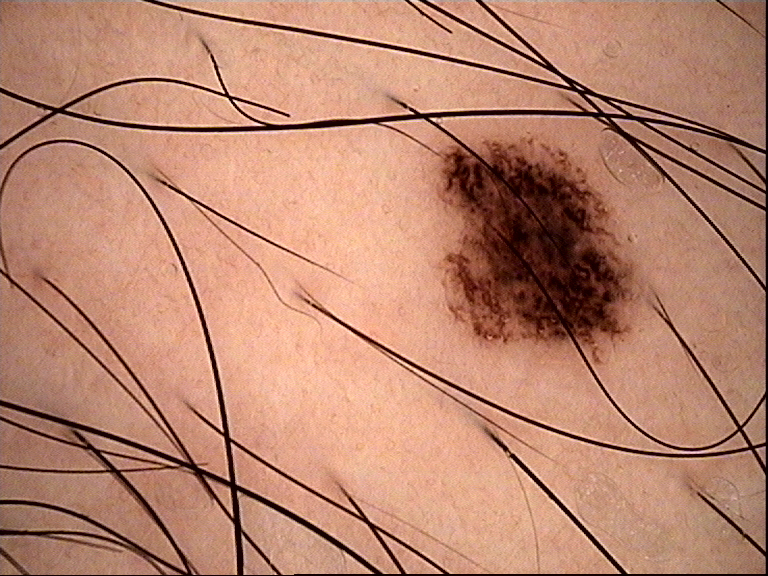Consistent with a benign lesion — a dysplastic junctional nevus.